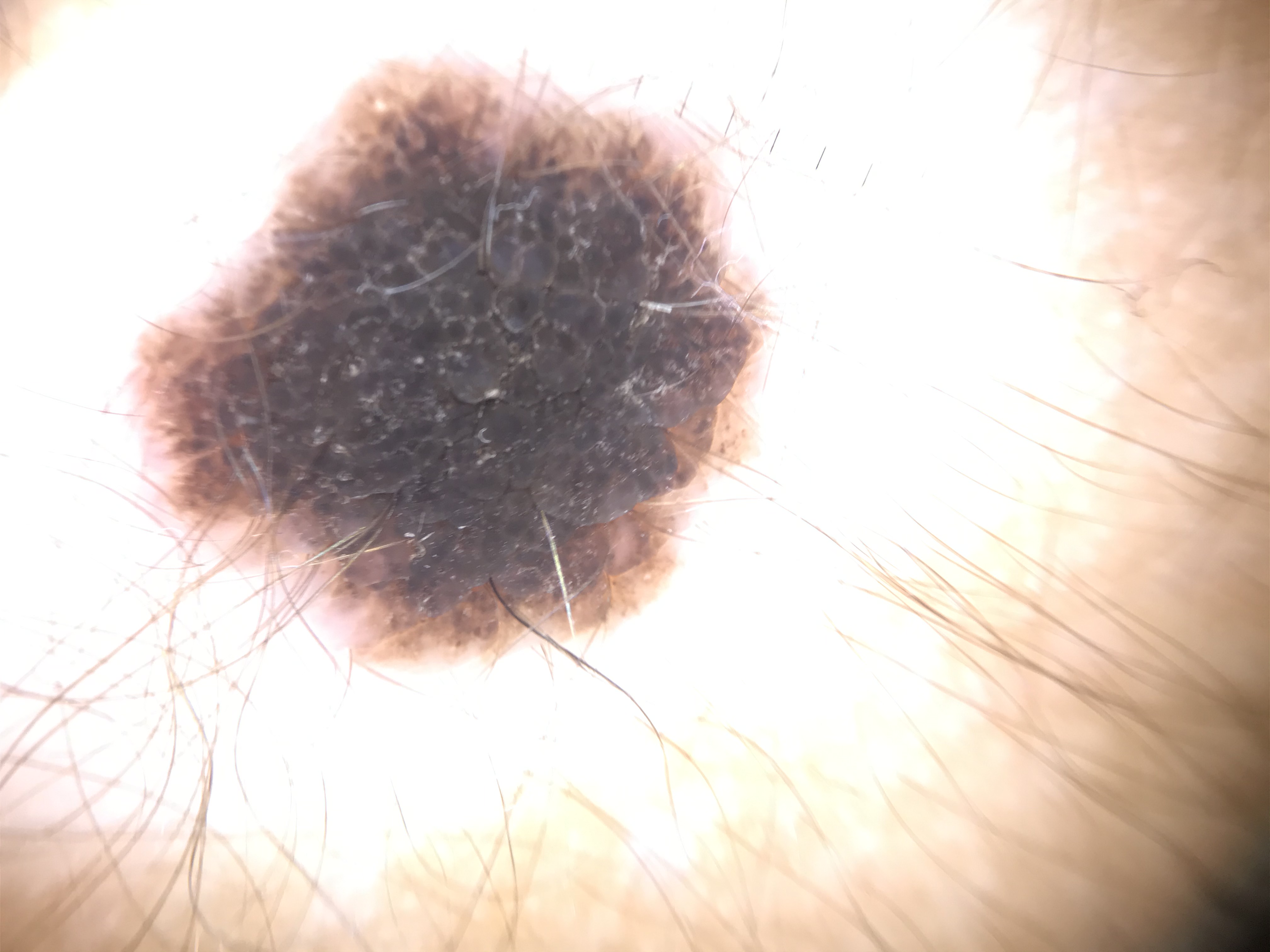Impression:
The diagnosis was a banal lesion — a congenital compound nevus.